A dermoscopic image of a skin lesion.
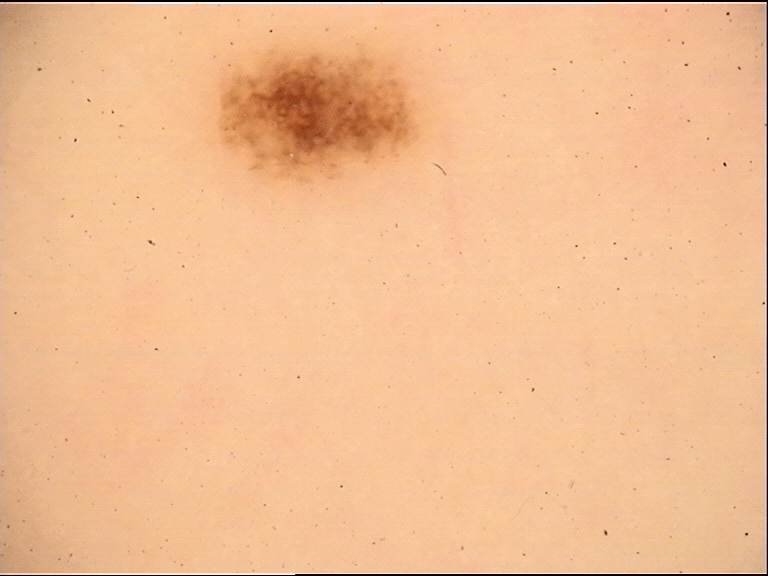class: junctional nevus (expert consensus)